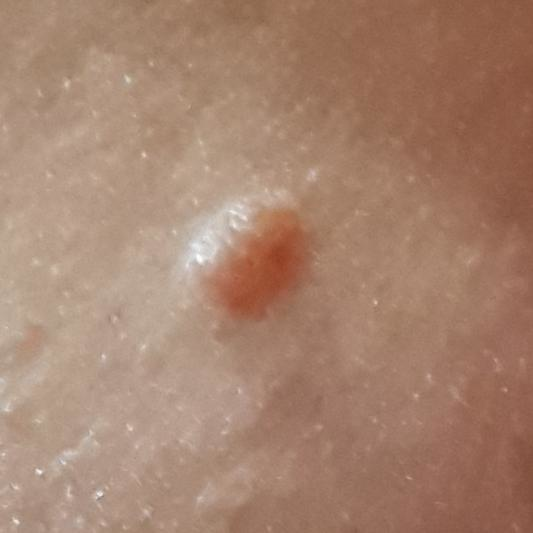Summary:
A clinical photograph of a skin lesion. A subject in their 40s. The lesion was found on the face. By the patient's account, the lesion is elevated.
Impression:
Consistent with a benign lesion — a nevus.